This is a close-up image · located on the head or neck · female contributor, age 30–39:
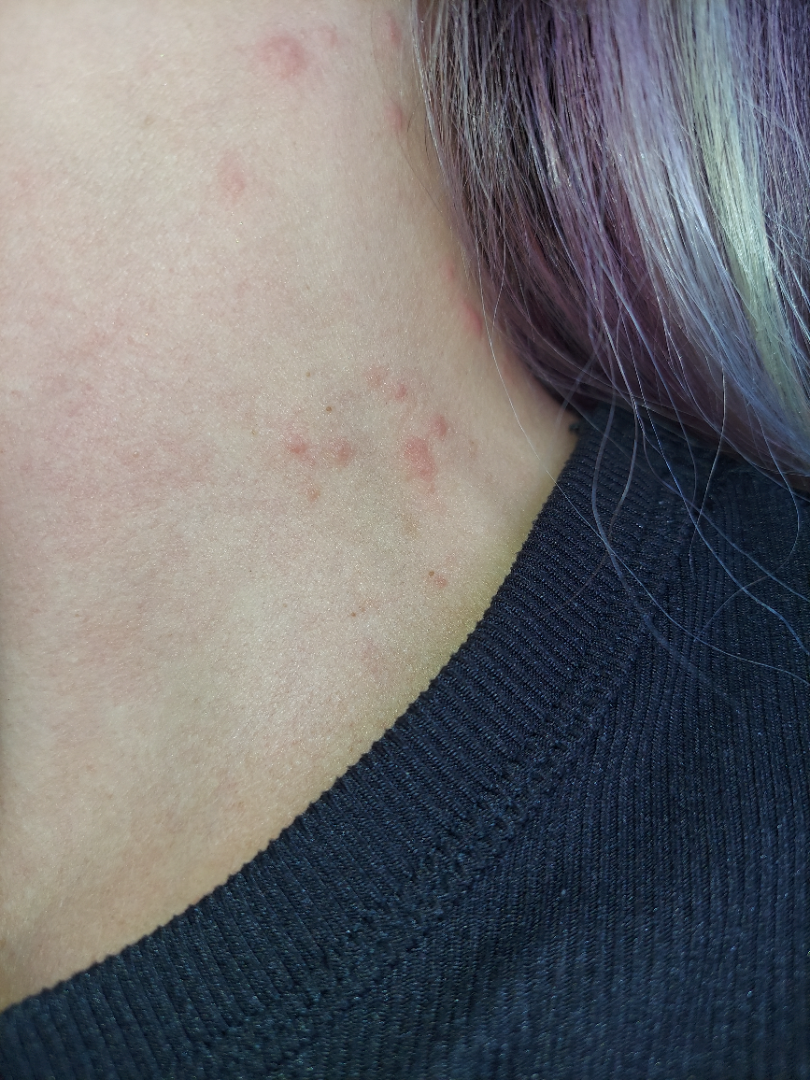Q: What was the assessment?
A: indeterminate from the photograph